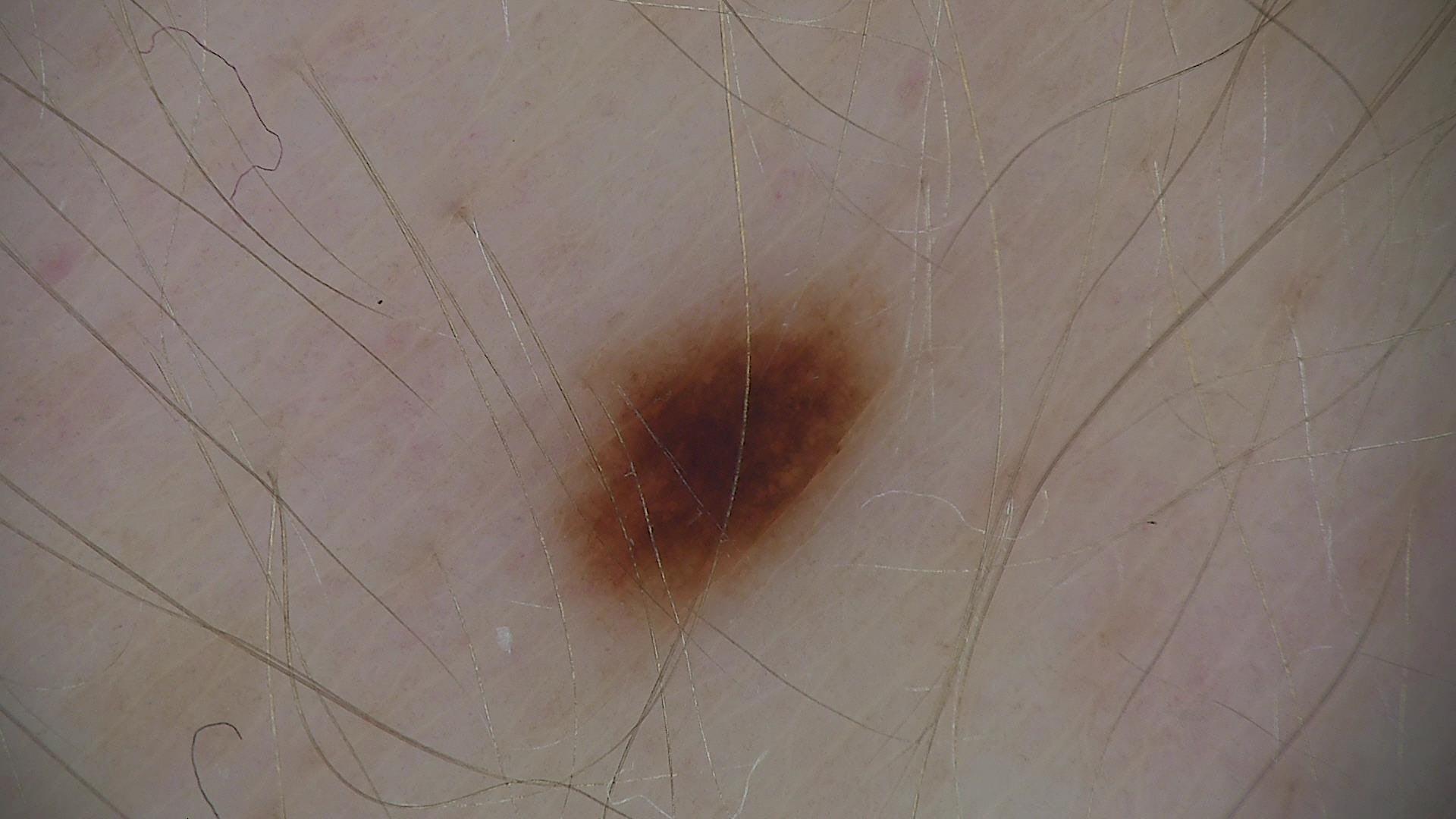A dermoscopic close-up of a skin lesion. Classified as a benign lesion — a dysplastic junctional nevus.